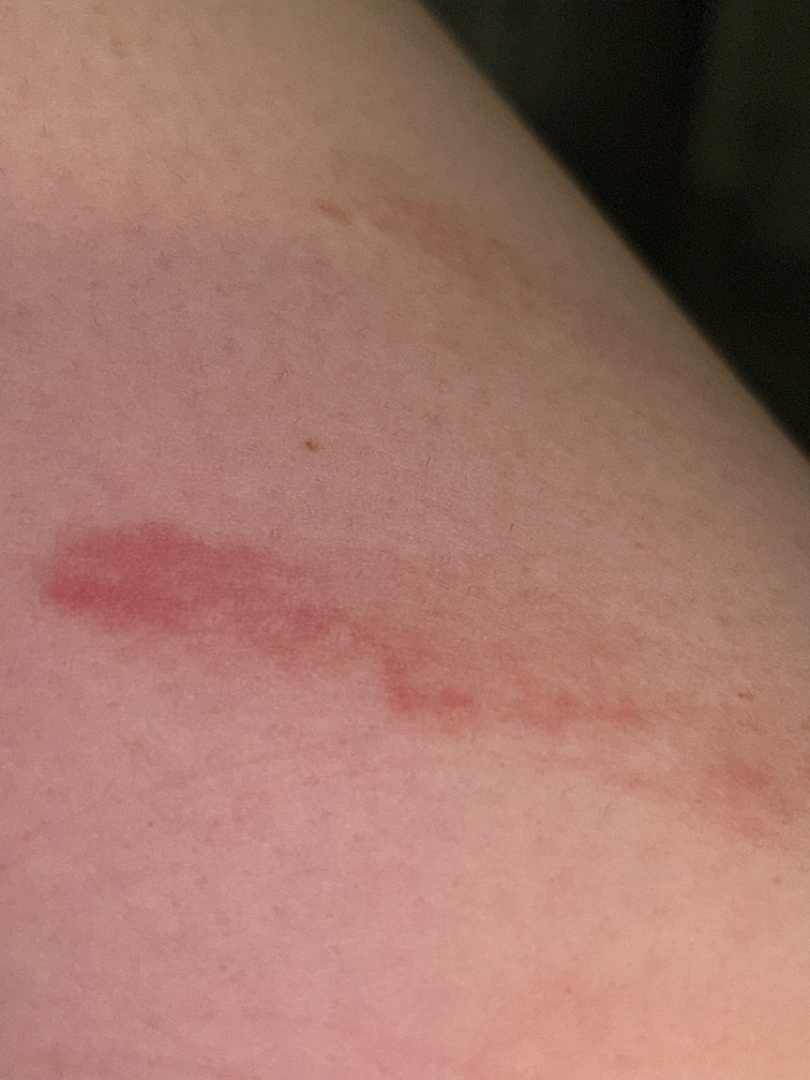Q: What was the assessment?
A: ungradable on photographic review
Q: Patient demographics?
A: female, age 18–29
Q: Patient's own categorization?
A: a rash
Q: What is the lesion texture?
A: raised or bumpy and flat
Q: How long has this been present?
A: less than one week
Q: Where on the body?
A: leg
Q: Image view?
A: close-up
Q: What symptoms does the patient report?
A: none reported